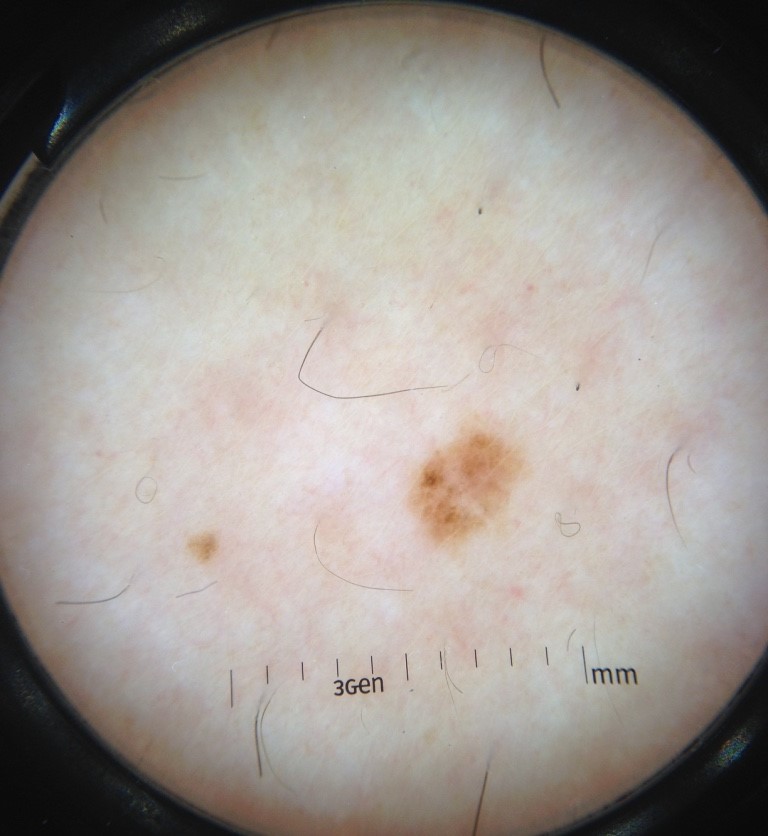Impression: Labeled as a junctional nevus.